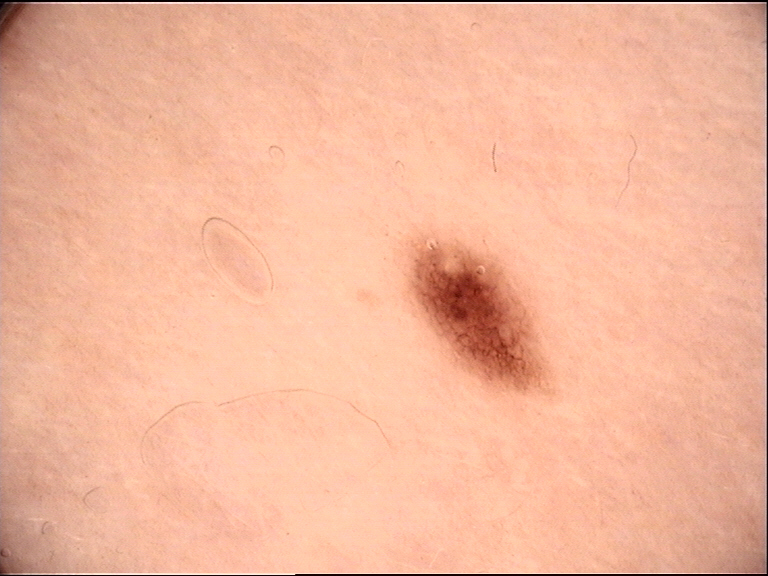Case:
- imaging · dermoscopy
- diagnosis · dysplastic junctional nevus (expert consensus)